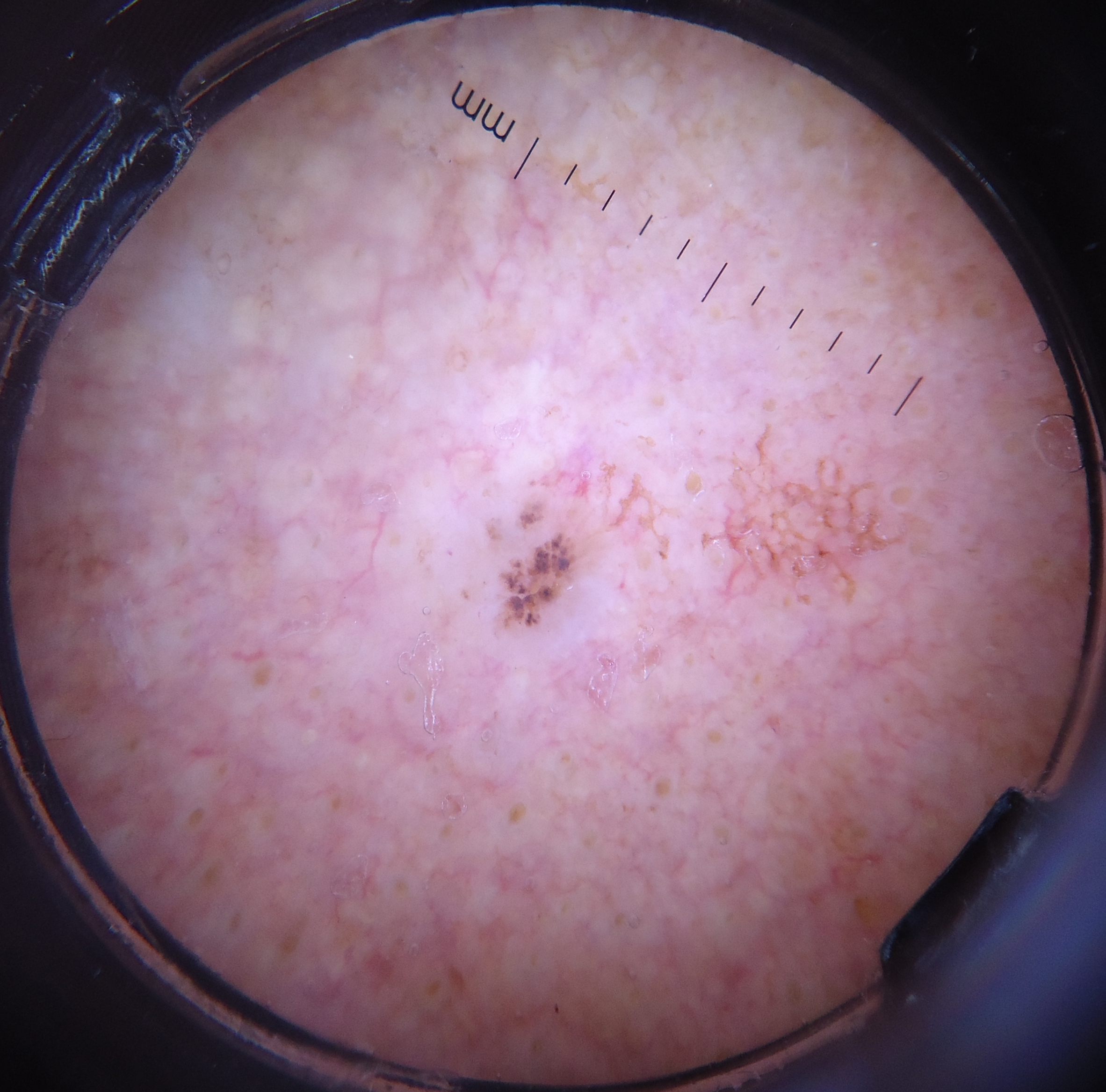Dermoscopy of a skin lesion.
The biopsy diagnosis was a keratinocytic, malignant lesion — a basal cell carcinoma.